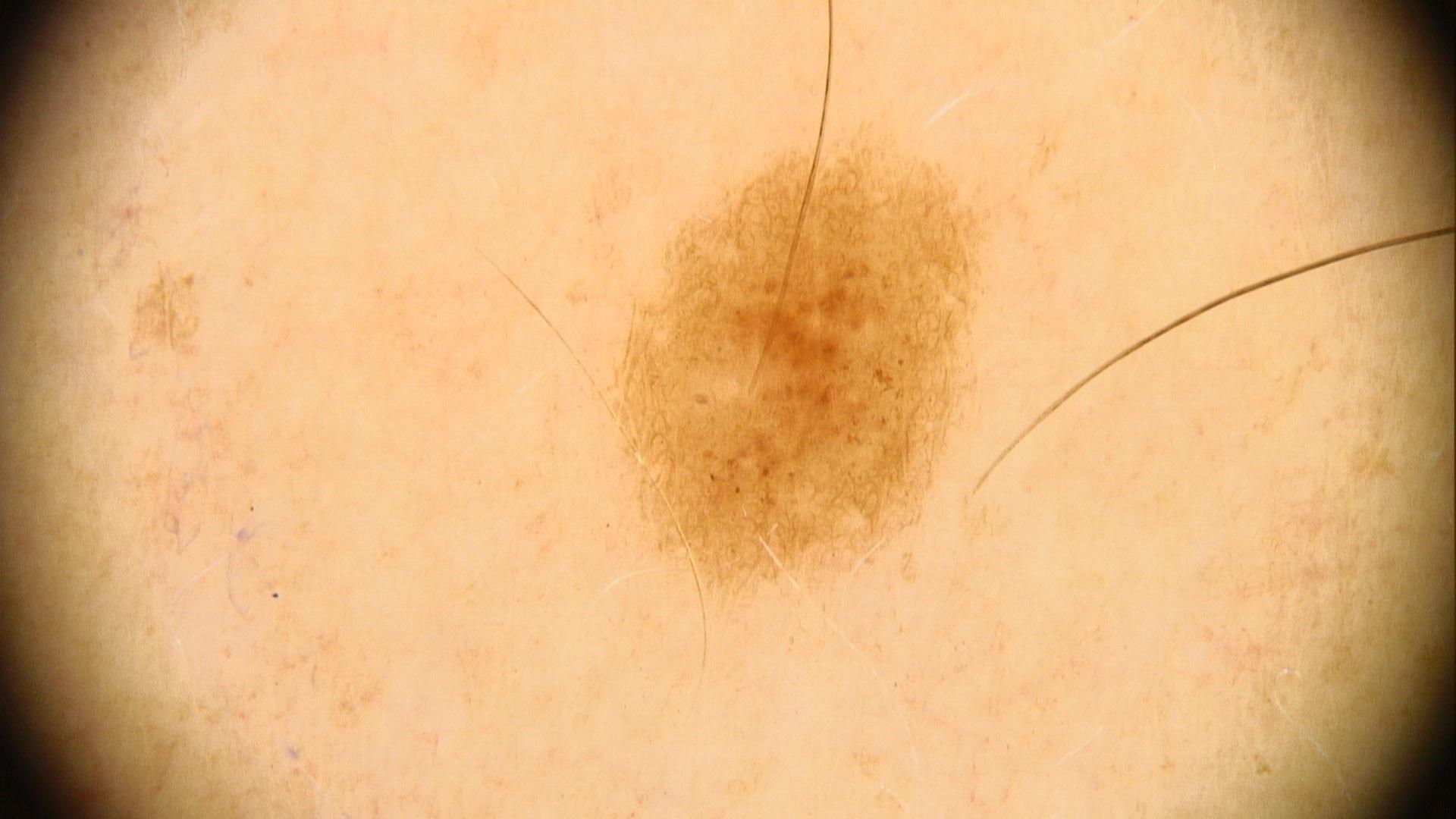A male patient in their 40s. A contact-polarized dermoscopy image of a skin lesion. The clinical impression was a nevus.